A patient in their mid-70s · a smartphone photograph of a skin lesion.
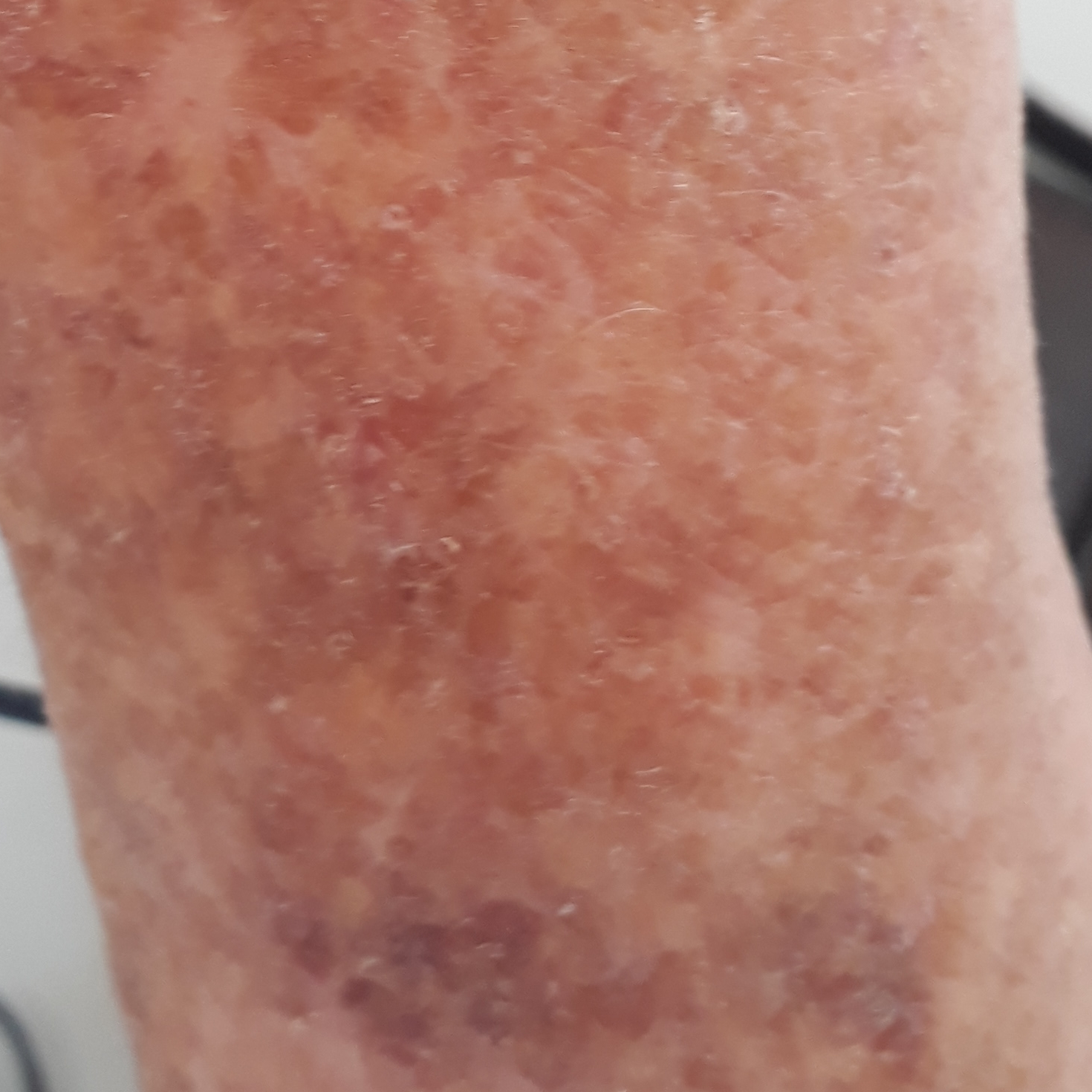Patient and lesion: The lesion is on a forearm. The patient describes that the lesion is elevated. Conclusion: The clinical impression was an actinic keratosis.